The photograph was taken at a distance; the arm and back of the hand are involved; male contributor, age 18–29:
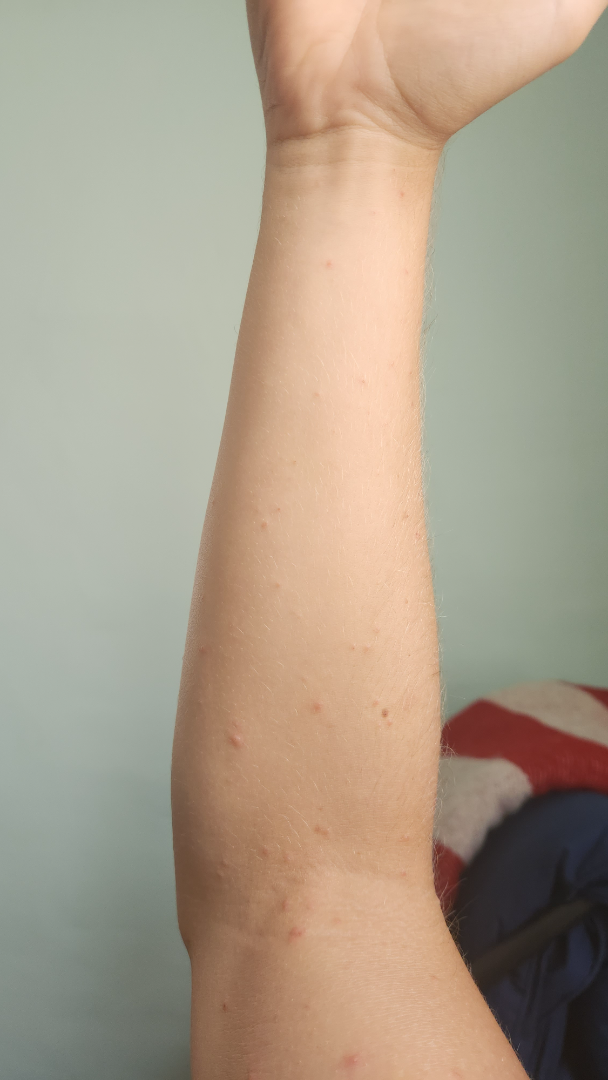Findings: Scabies (favored); Insect Bite (considered); Hypersensitivity (considered).